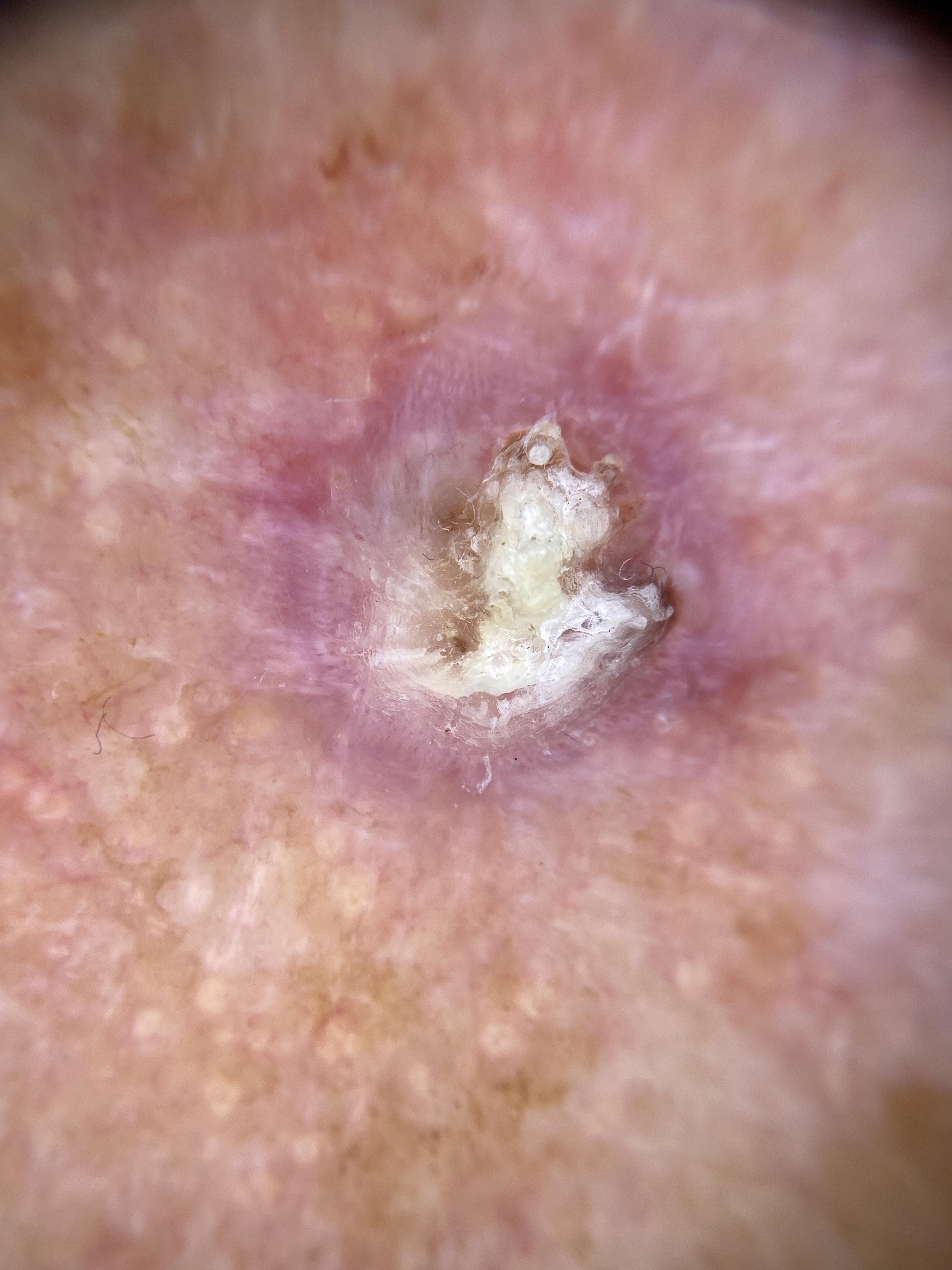A dermoscopic photograph of a skin lesion.
The lesion is on the head or neck.
Histopathological examination showed a squamous cell carcinoma.